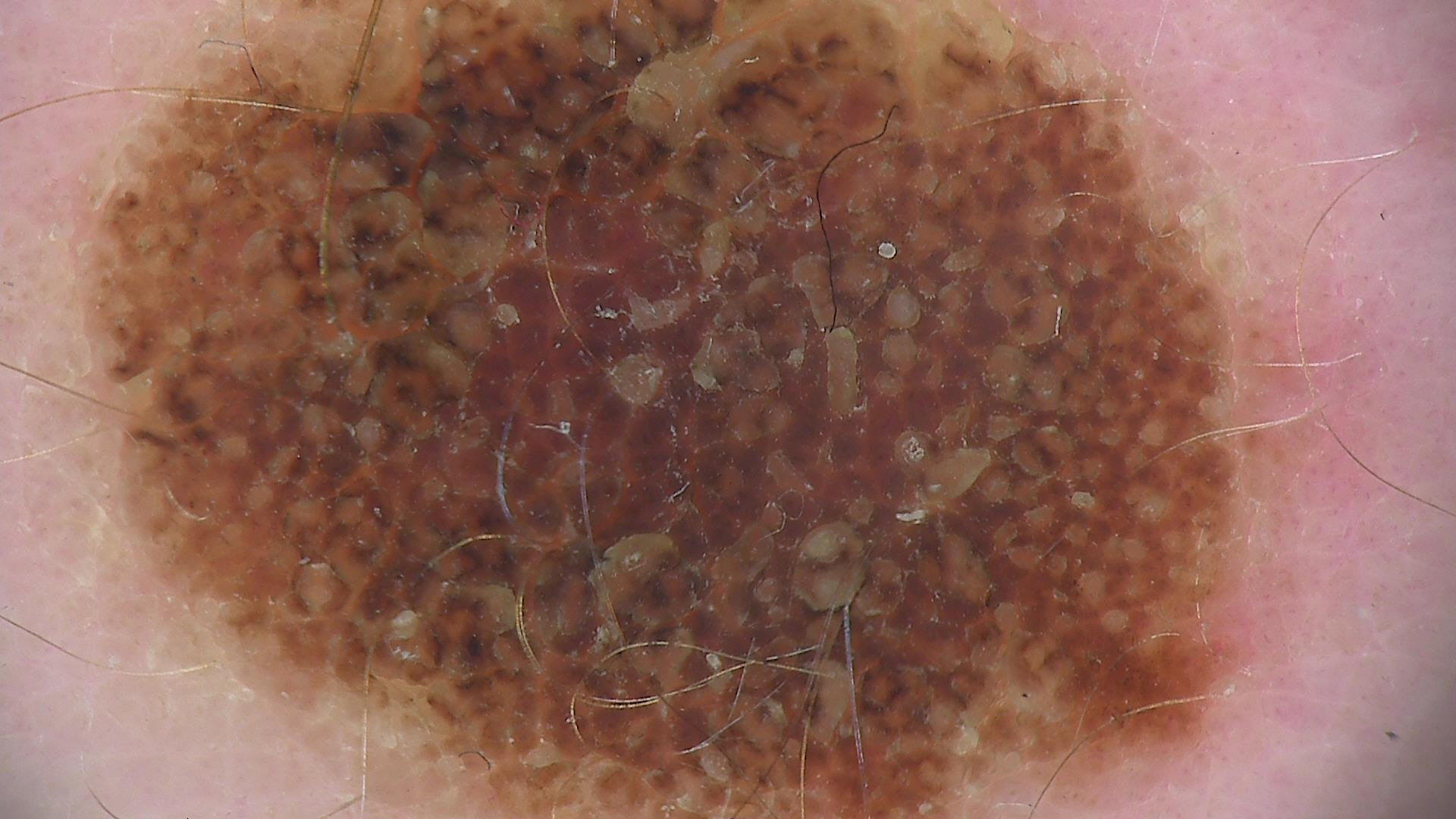Classified as a banal lesion — a compound nevus.